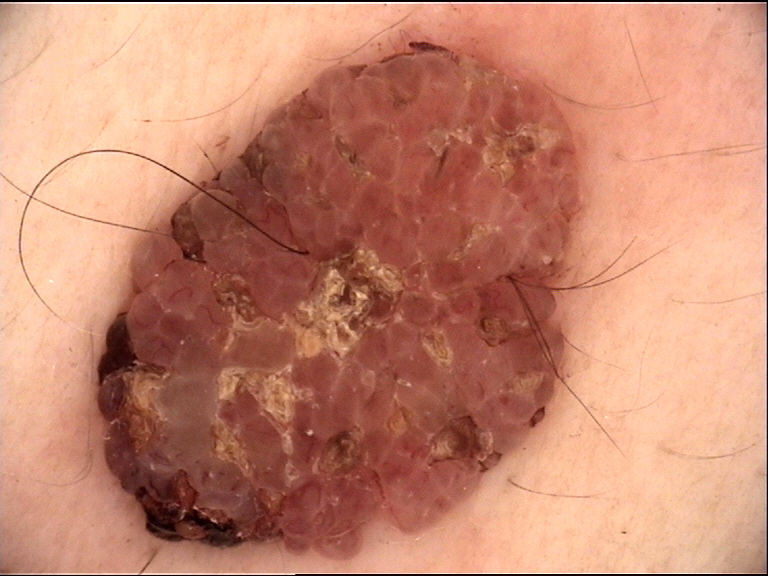A dermoscopy image of a single skin lesion. Classified as a banal lesion — a dermal nevus.